The patient describes having a moderate number of moles. A male subject 72 years old. The patient says their skin tans without first burning. A clinical photograph of a skin lesion. Imaged for a research study, with no referral diagnosis recorded: 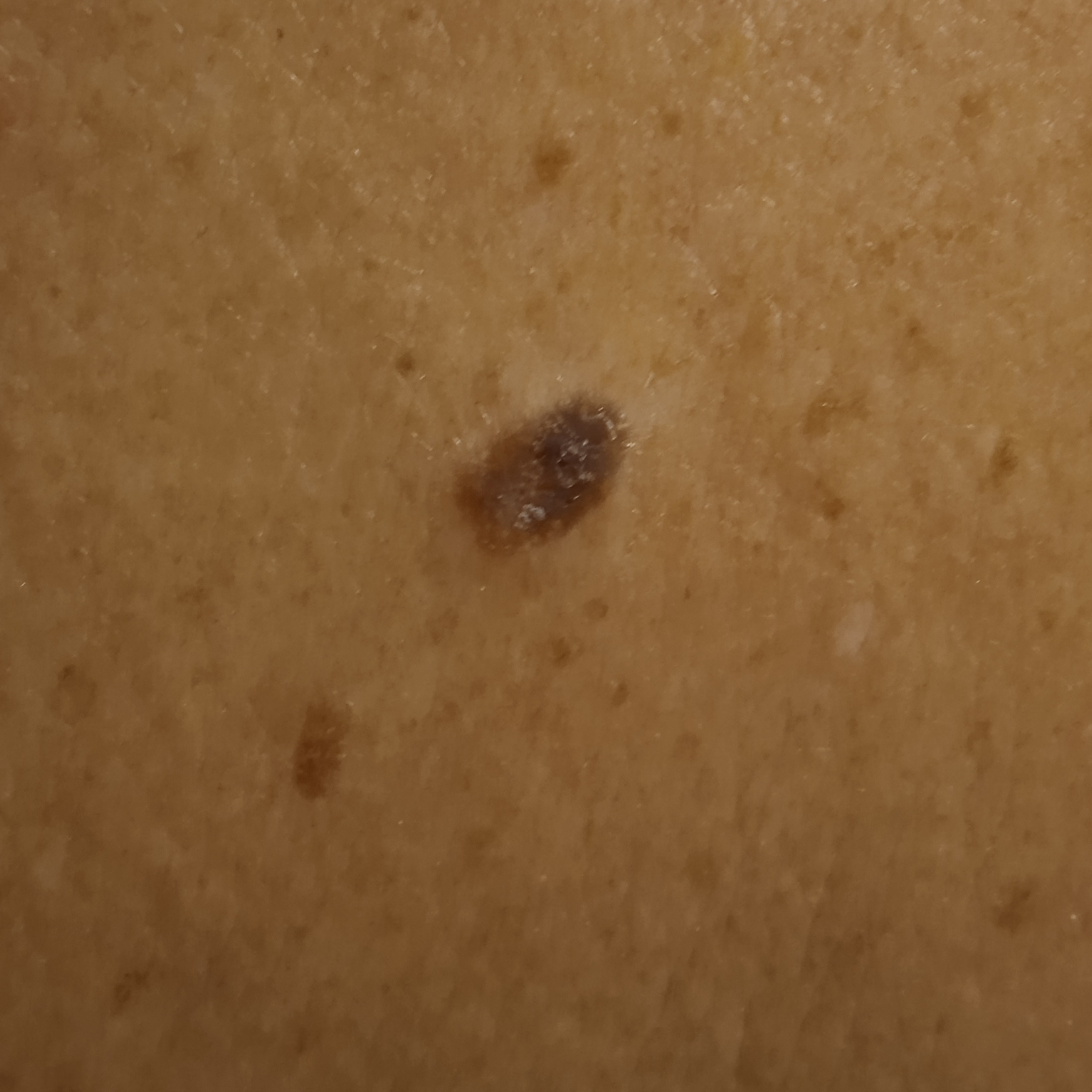Measuring roughly 8.1 mm. The lesion was assessed as a seborrheic keratosis.